A skin lesion imaged with a dermatoscope.
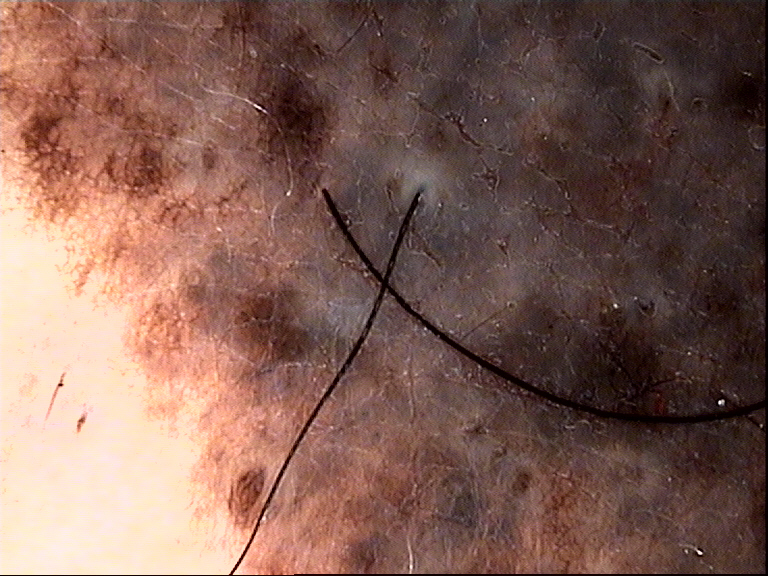{"lesion_type": {"main_class": "banal", "pattern": "compound"}, "diagnosis": {"name": "congenital compound nevus", "code": "ccb", "malignancy": "benign", "super_class": "melanocytic", "confirmation": "expert consensus"}}